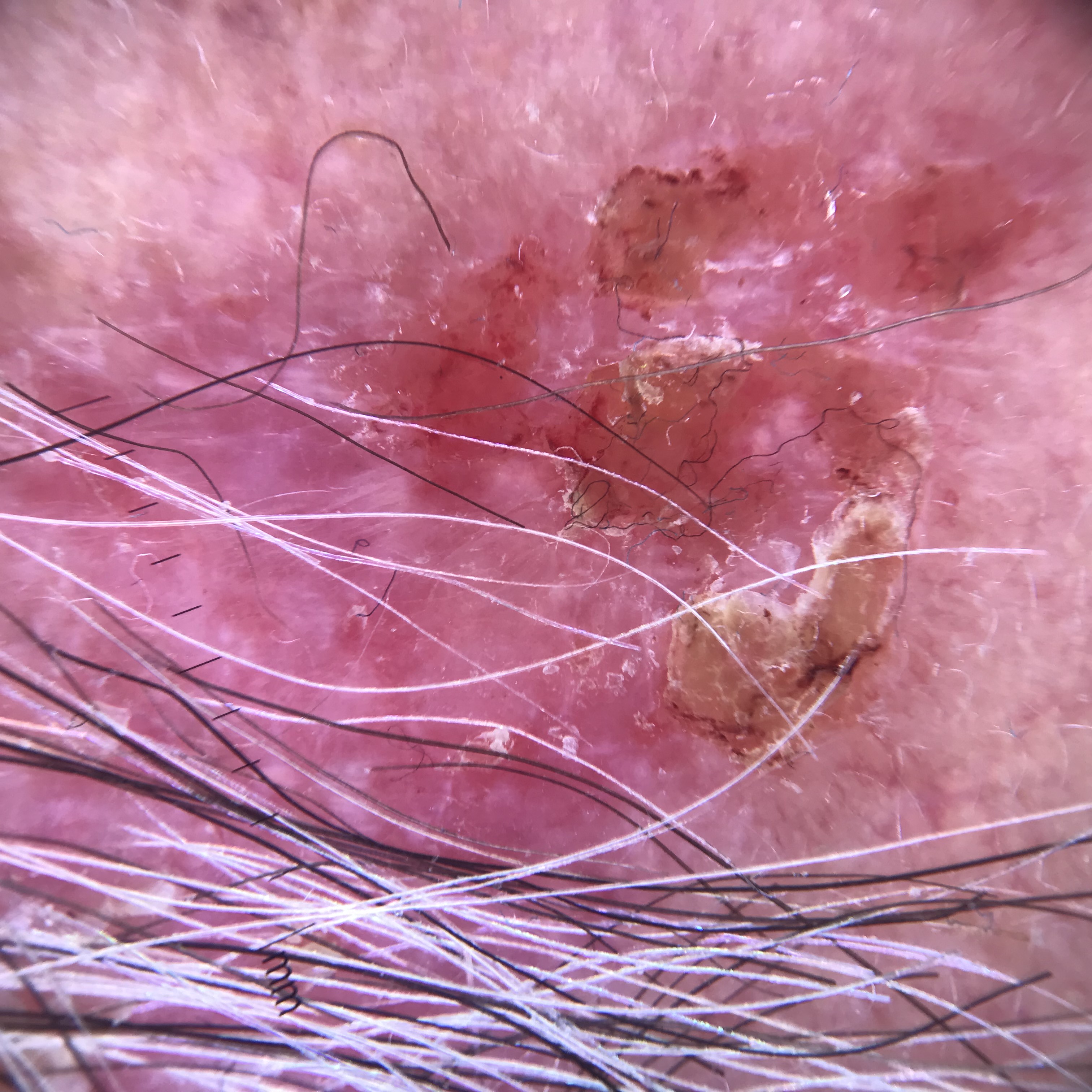image=dermatoscopy | subtype=keratinocytic | class=Bowen's disease (biopsy-proven).